A dermoscopic image of a skin lesion.
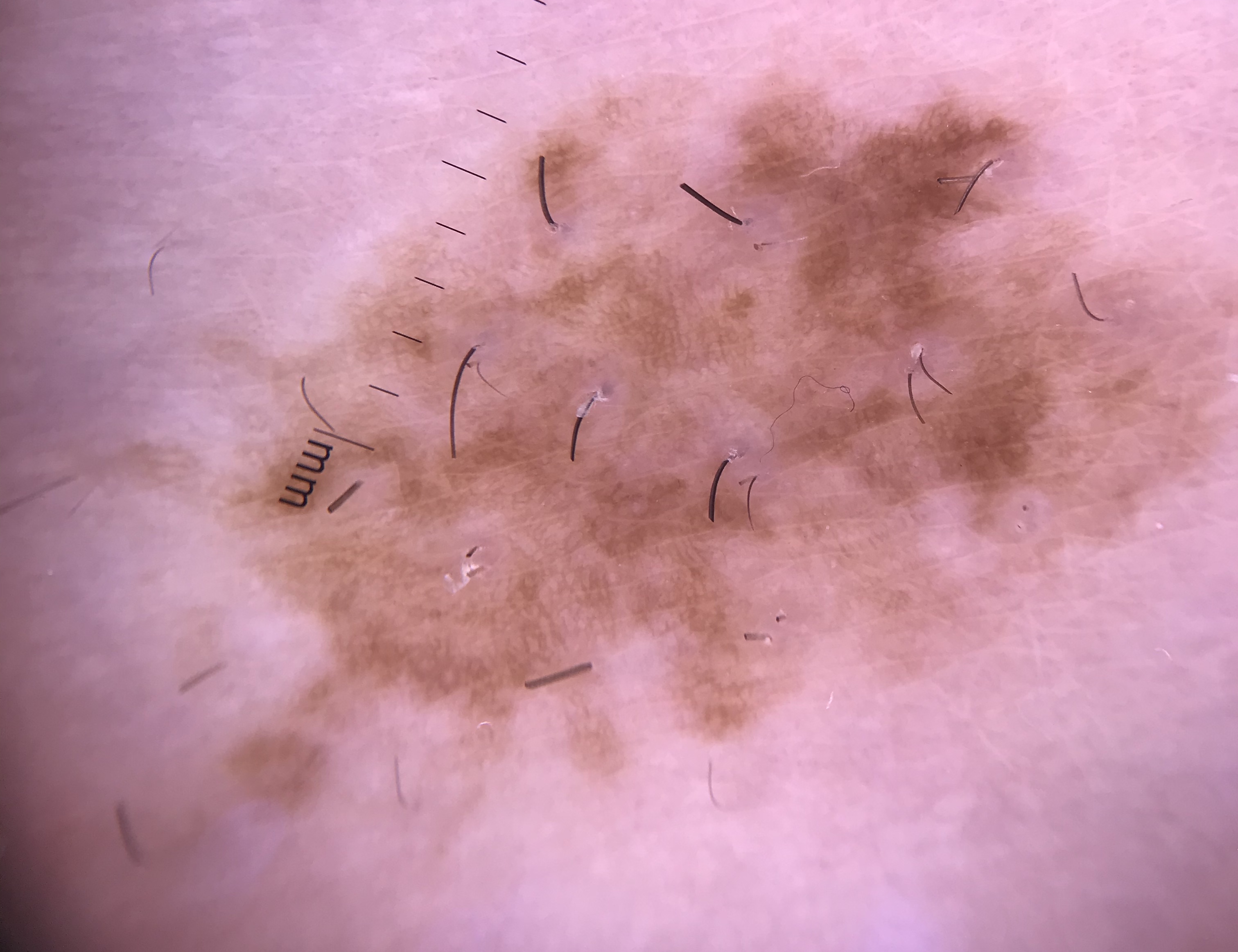lesion_type:
  main_class: banal
  pattern: compound
diagnosis:
  name: congenital compound nevus
  code: ccb
  malignancy: benign
  super_class: melanocytic
  confirmation: expert consensus